Imaged for a research study, with no referral diagnosis recorded. The patient describes having a moderate number of moles. A skin lesion imaged with a dermatoscope:
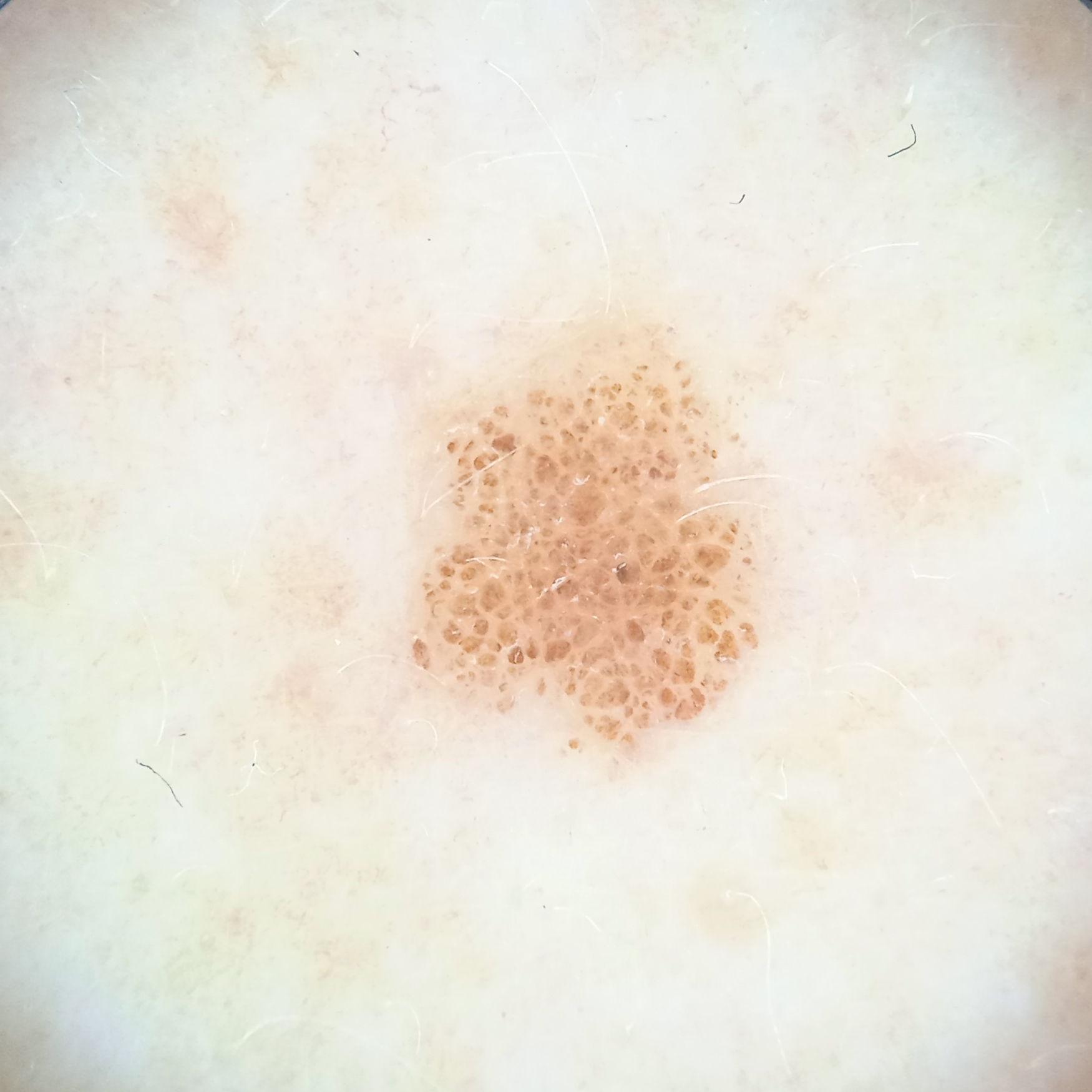Dermatologist review favored a melanocytic nevus.